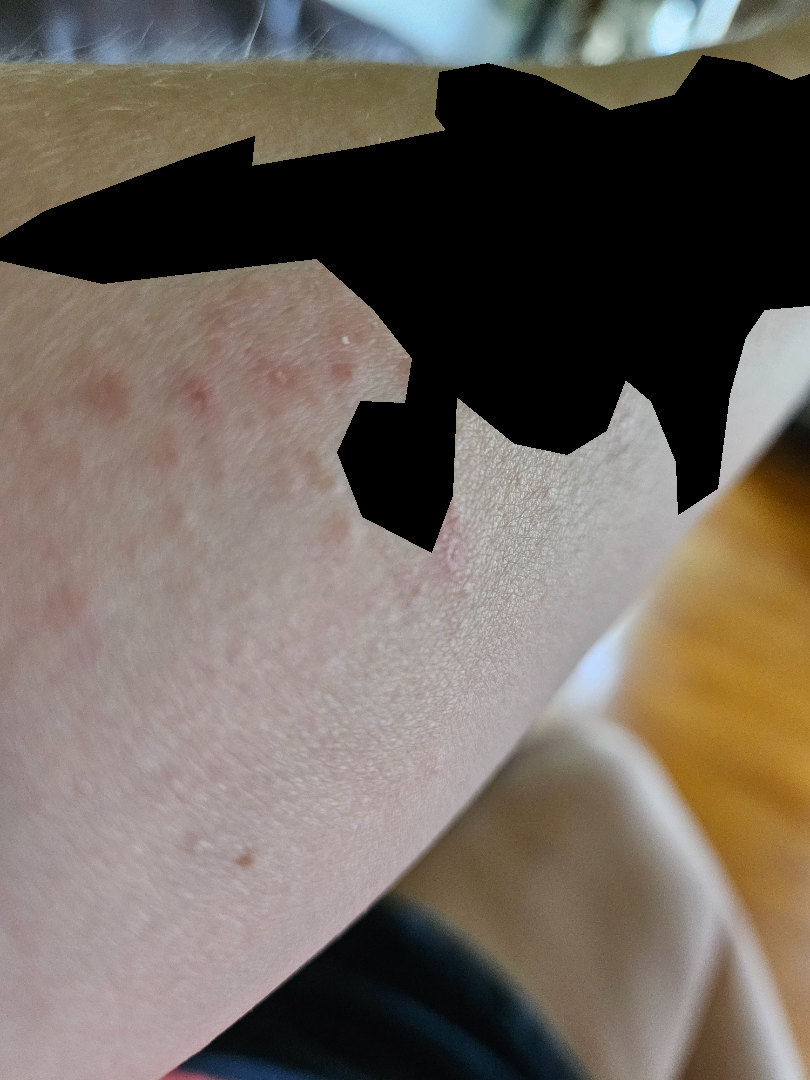{"assessment": "indeterminate from the photograph"}